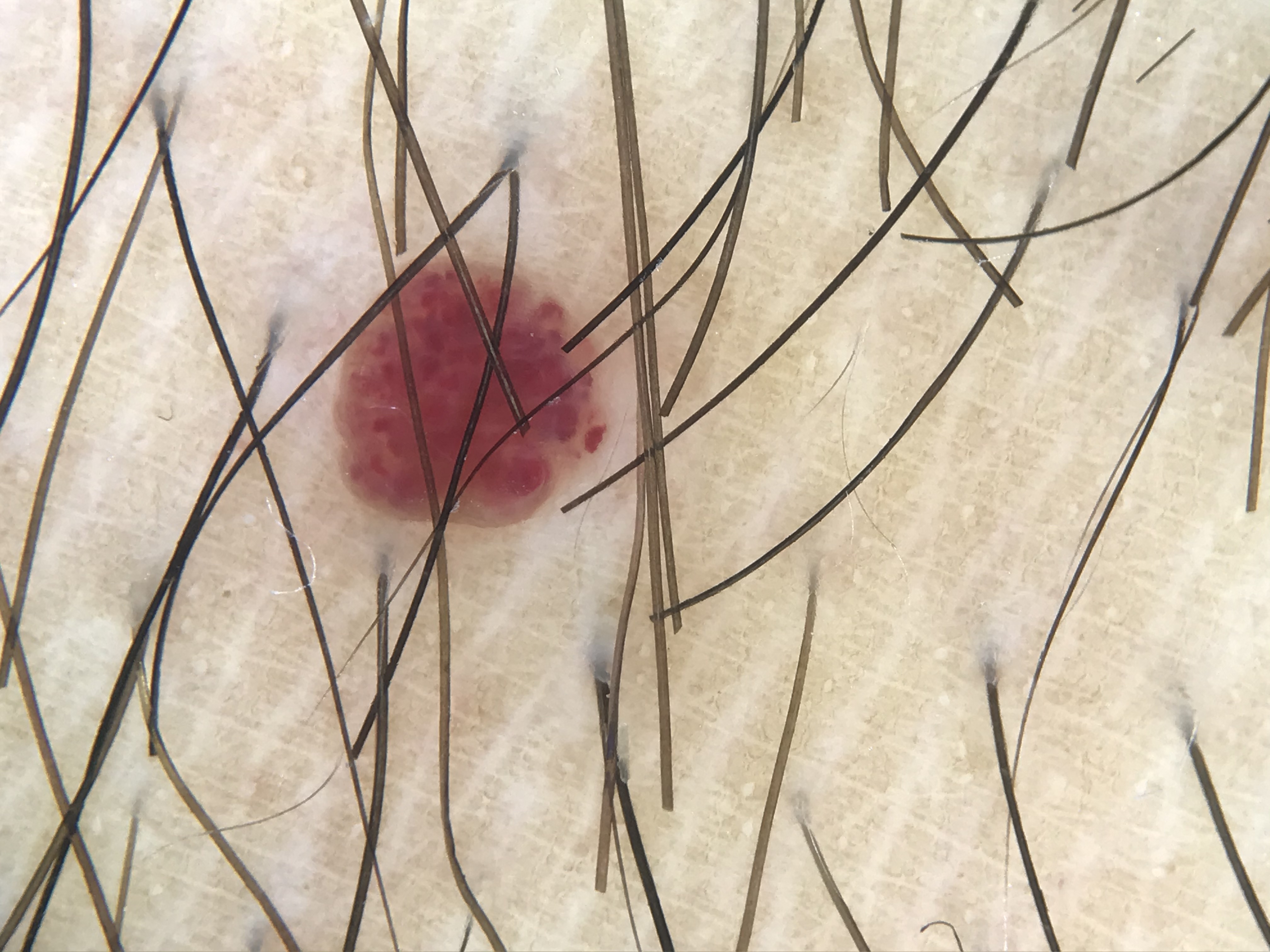image: dermoscopy
lesion_type:
  main_class: vascular
diagnosis:
  name: hemangioma
  code: ha
  malignancy: benign
  super_class: non-melanocytic
  confirmation: expert consensus